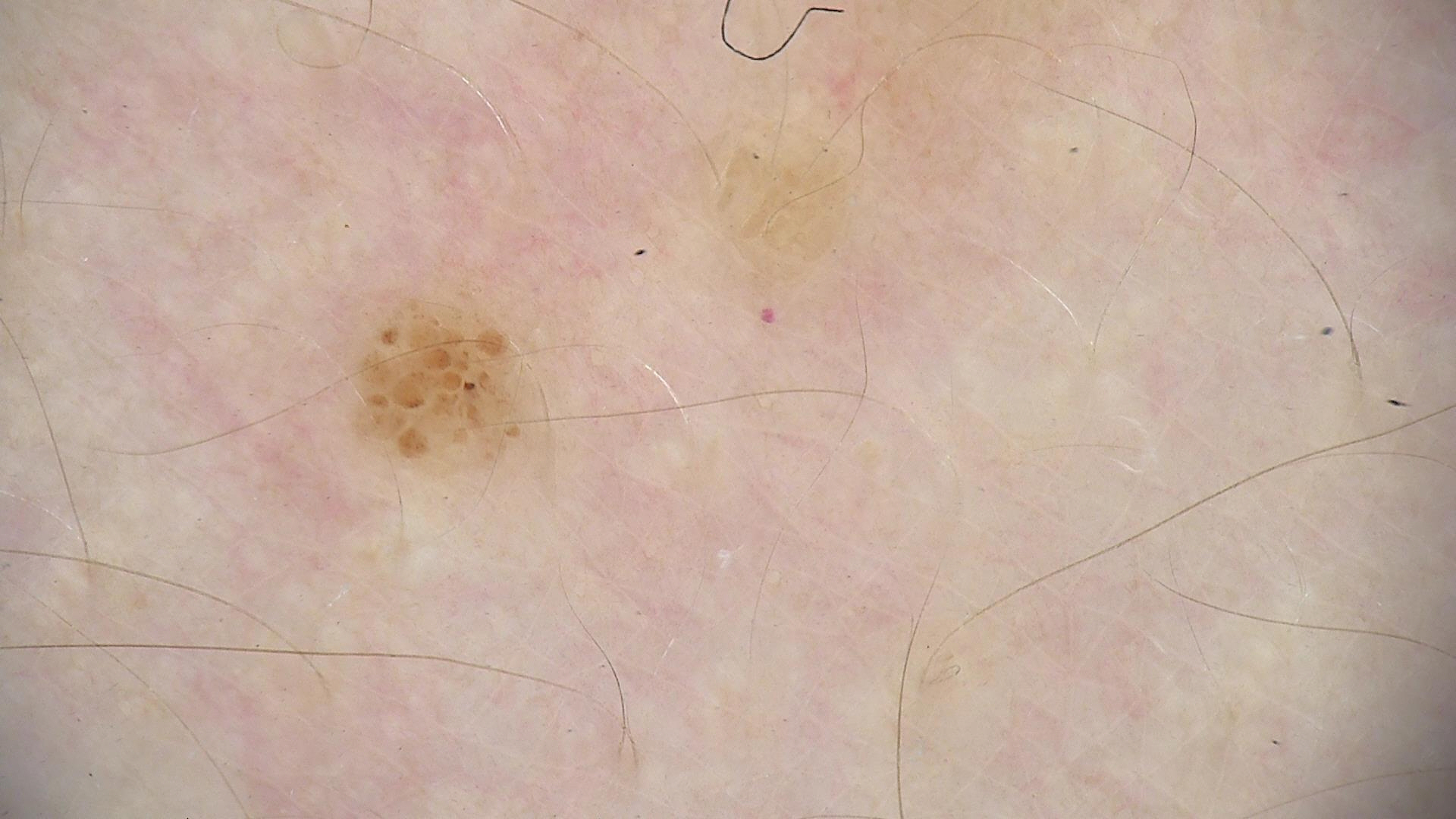A dermoscopic image of a skin lesion. Classified as a compound nevus.